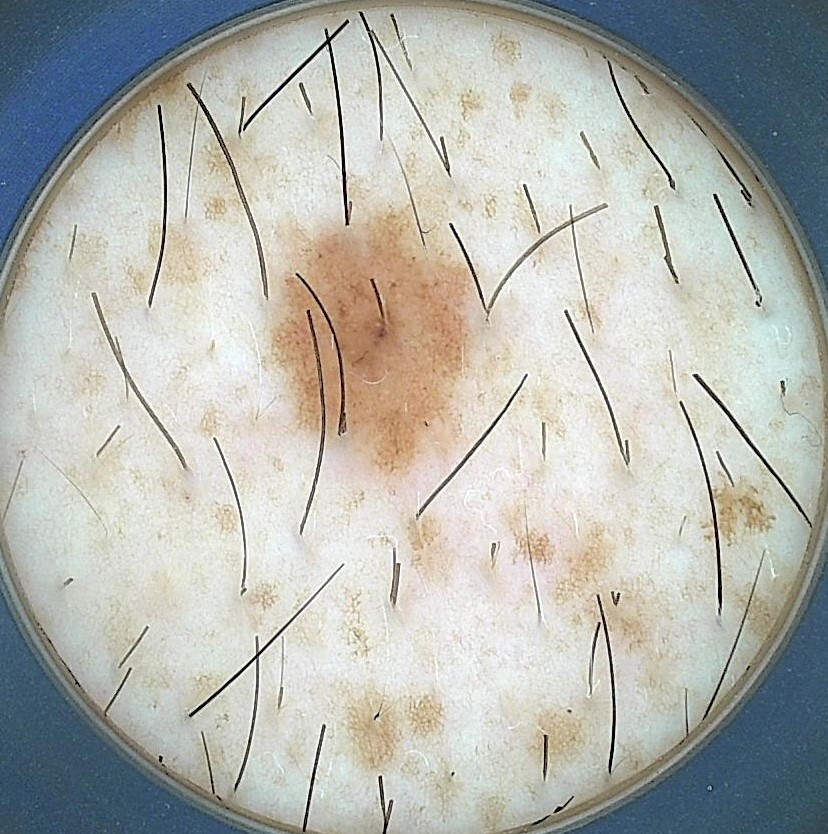Diagnosed as a dysplastic junctional nevus.